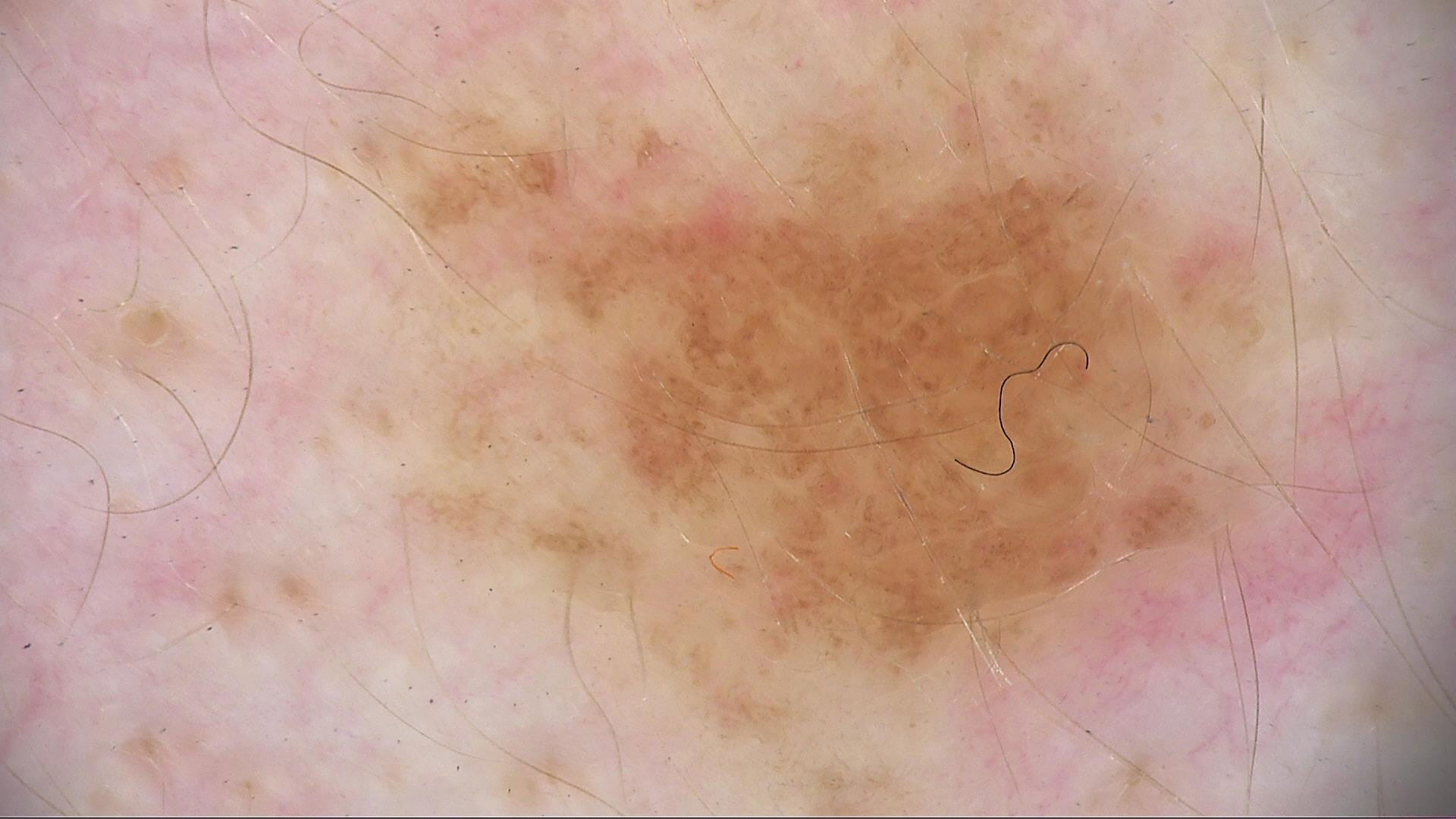imaging: dermatoscopy, label: compound nevus (expert consensus).